Located on the top or side of the foot, leg and arm · the photograph was taken at a distance · the patient reports the lesion is raised or bumpy · reported duration is less than one week: 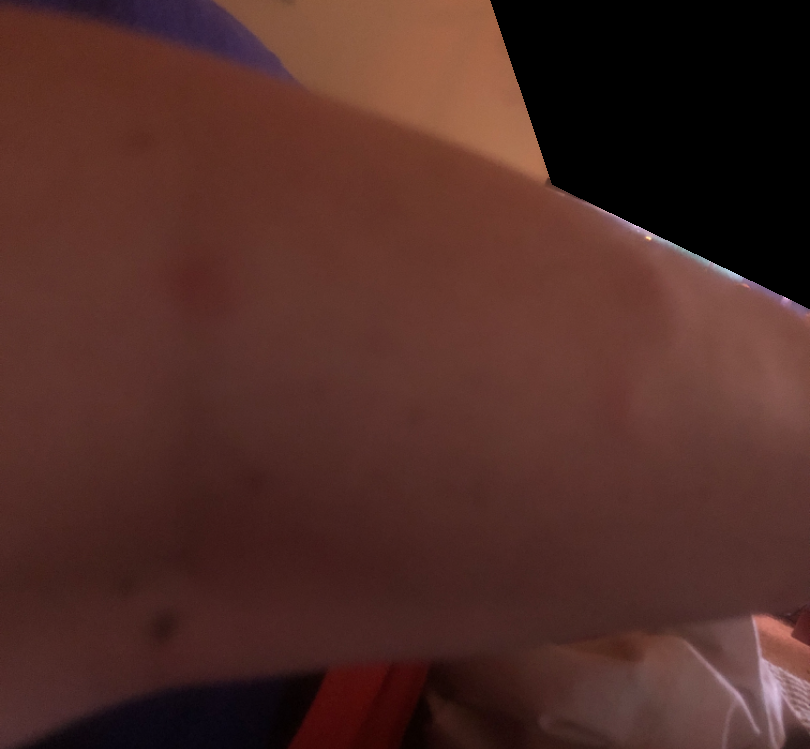<dermatology_case>
  <assessment>ungradable on photographic review</assessment>
</dermatology_case>